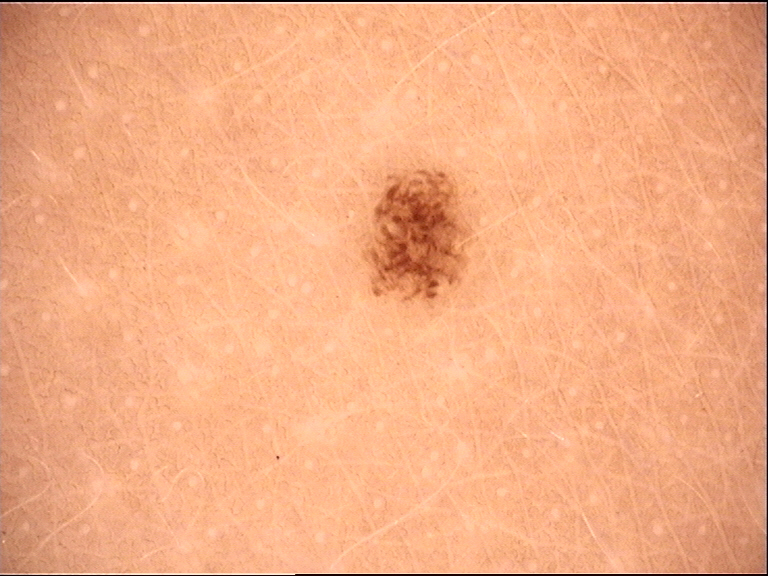Findings:
- diagnostic label — dysplastic junctional nevus (expert consensus)